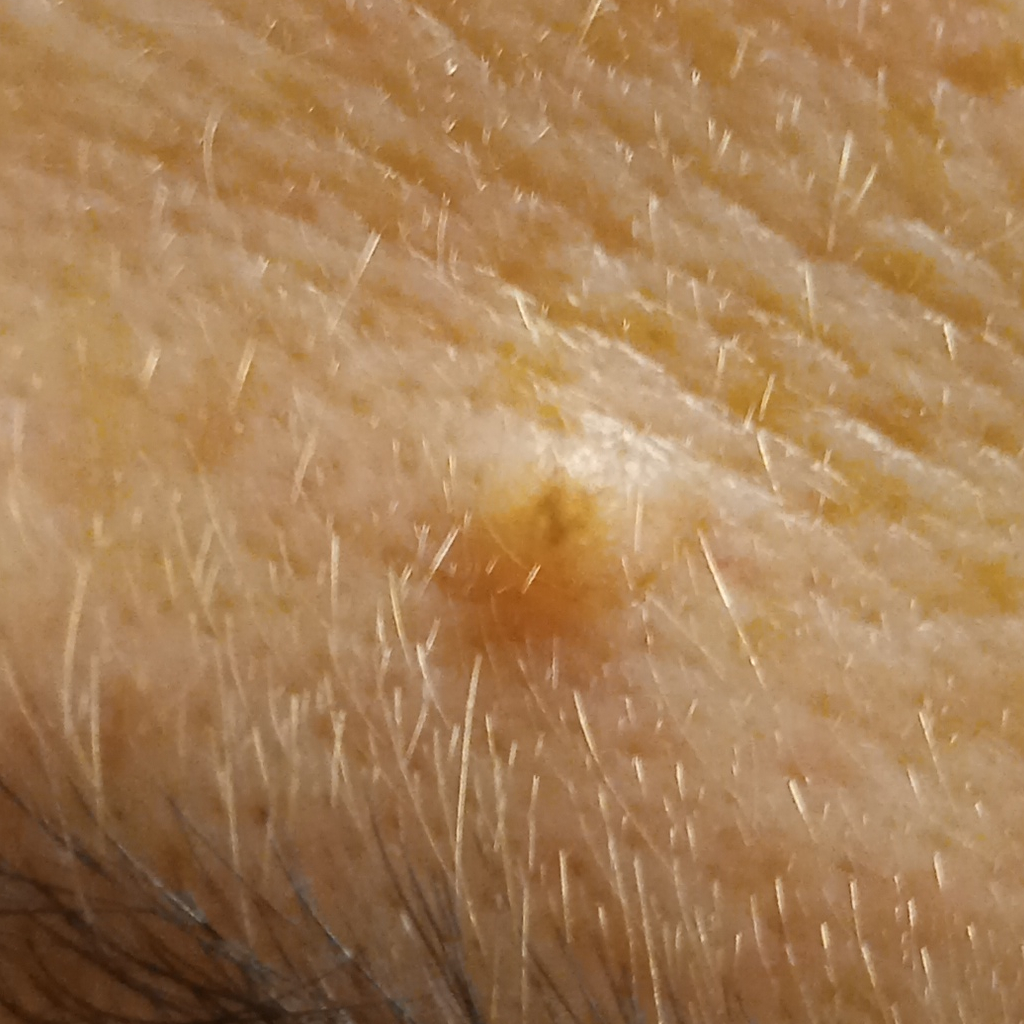Case summary:
A female patient 50 years of age. The patient says their skin reddens painfully with sun exposure. A clinical photograph showing a skin lesion. The referring clinician suspected melanoma. A moderate number of moles by the patient's own estimate. The lesion involves the face. The lesion measures approximately 1.8 mm.
Conclusion:
The diagnostic impression was a melanocytic nevus.